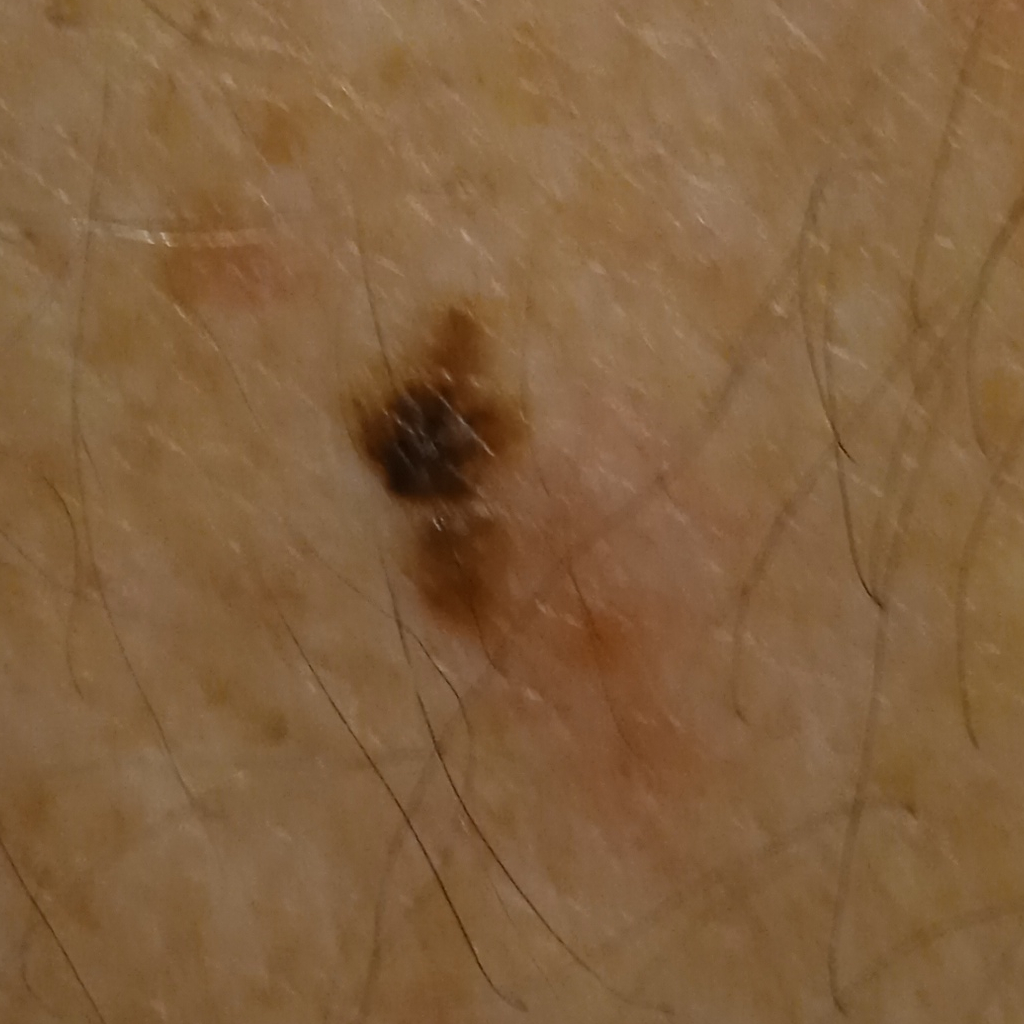Clinical context: A clinical photograph of a skin lesion. A male subject 76 years of age. Acquired for a research image collection, with no referral diagnosis. The patient says their skin reddens with sun exposure. Few moles overall by the patient's own estimate. On a questionnaire the patient reported a personal history of skin cancer and a personal history of cancer. The lesion is located on the back. Measuring roughly 7.8 mm. Conclusion: The lesion was assessed as a seborrheic keratosis.